The patient also reports fatigue and joint pain · located on the back of the hand · the contributor is a female aged 30–39 · this image was taken at an angle · skin tone: Fitzpatrick skin type II; lay reviewers estimated a Monk skin tone scale of 2 · texture is reported as raised or bumpy · reported lesion symptoms include bothersome appearance.
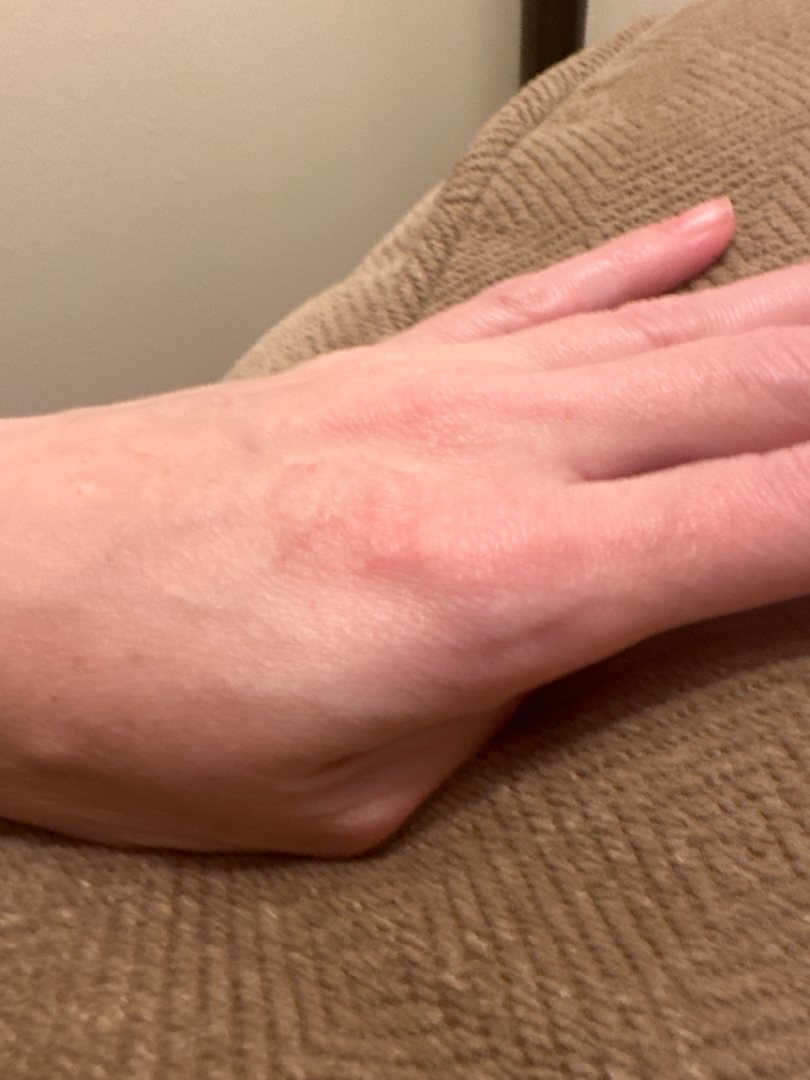Impression:
On teledermatology review: favoring Granuloma annulare; with consideration of Eczema; less probable is Tinea.